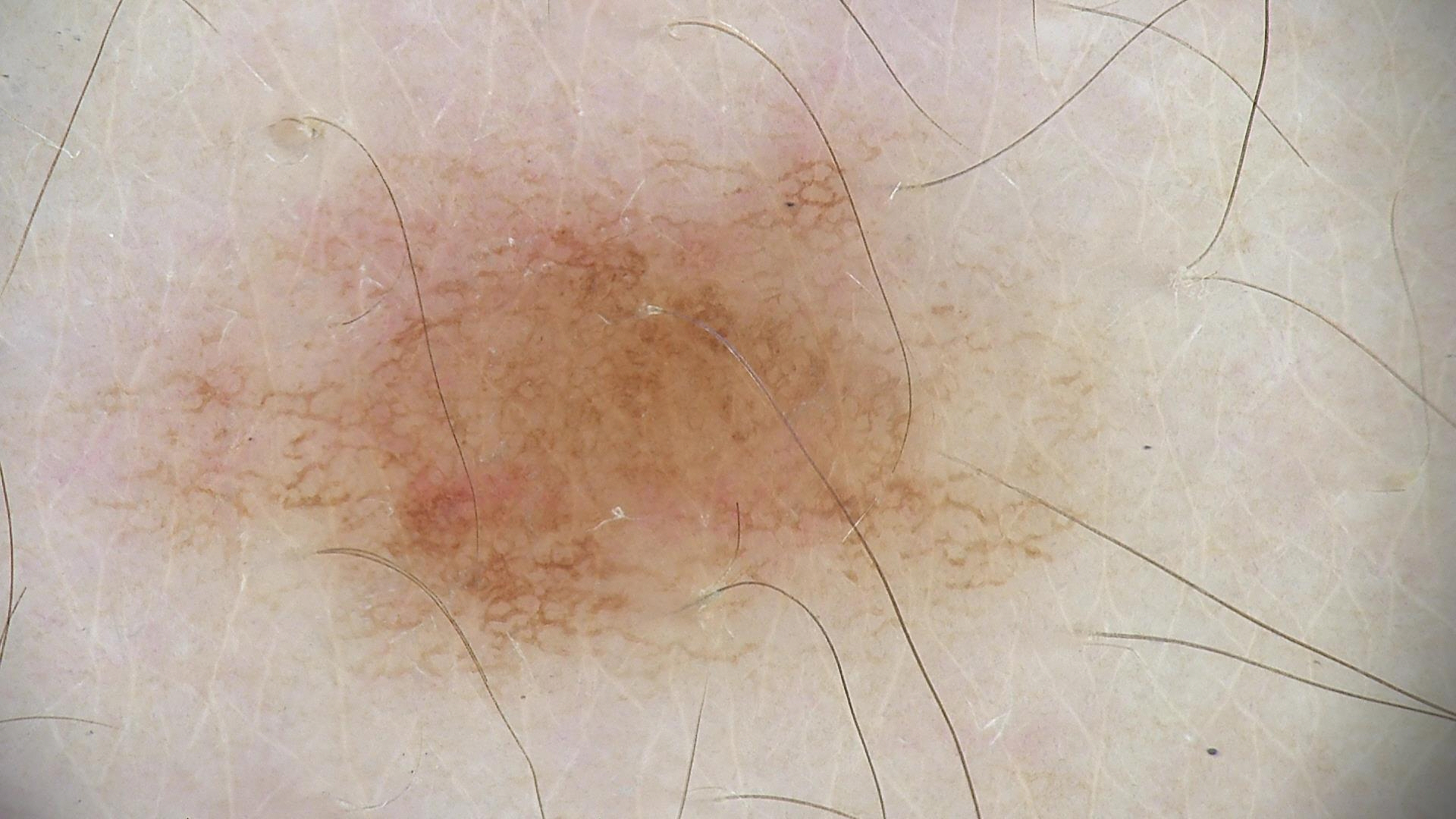| key | value |
|---|---|
| imaging | dermatoscopy |
| assessment | dysplastic junctional nevus (expert consensus) |